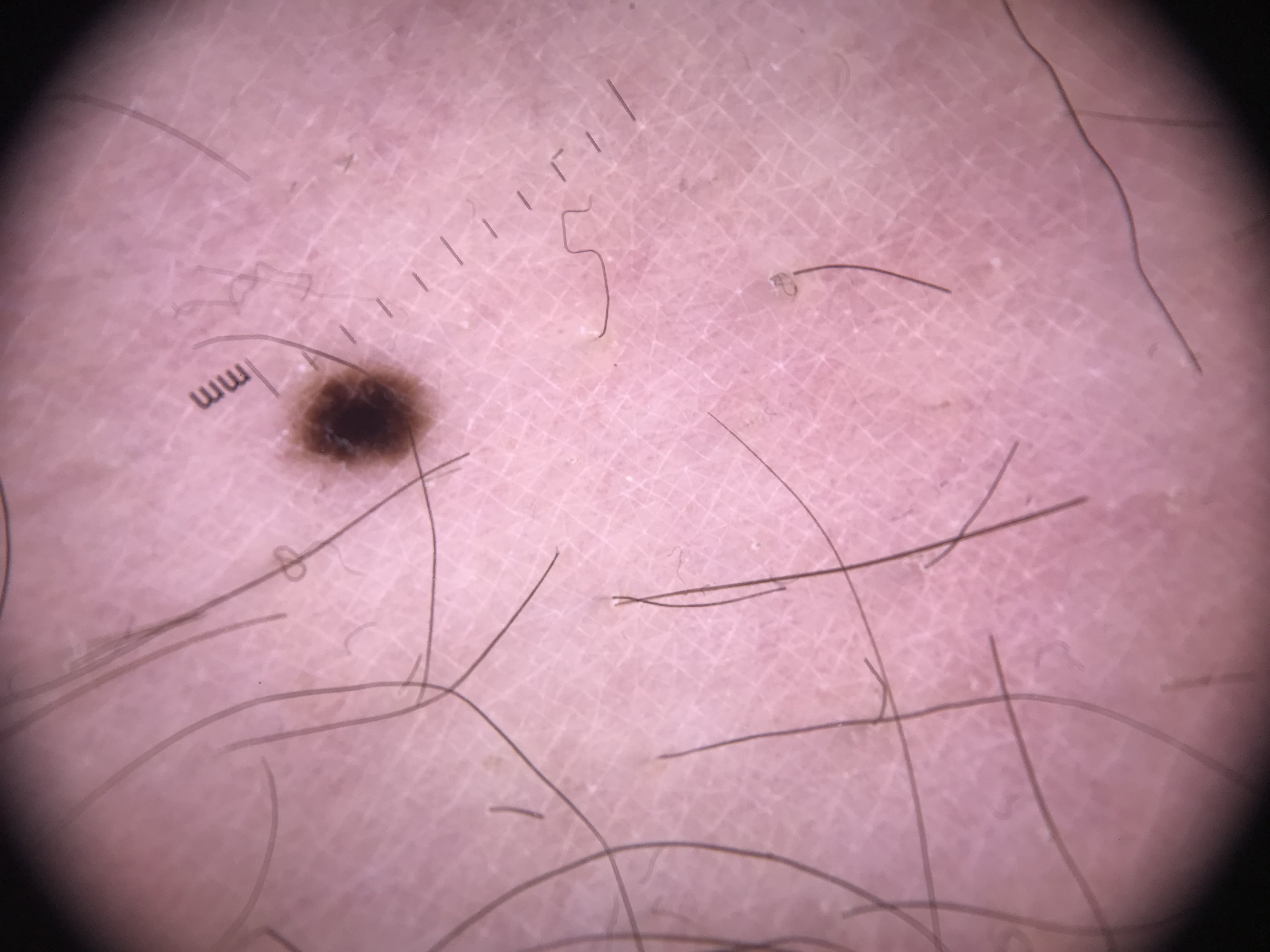Findings:
A dermoscopy image of a single skin lesion. This is a banal lesion.
Impression:
The diagnostic label was a junctional nevus.